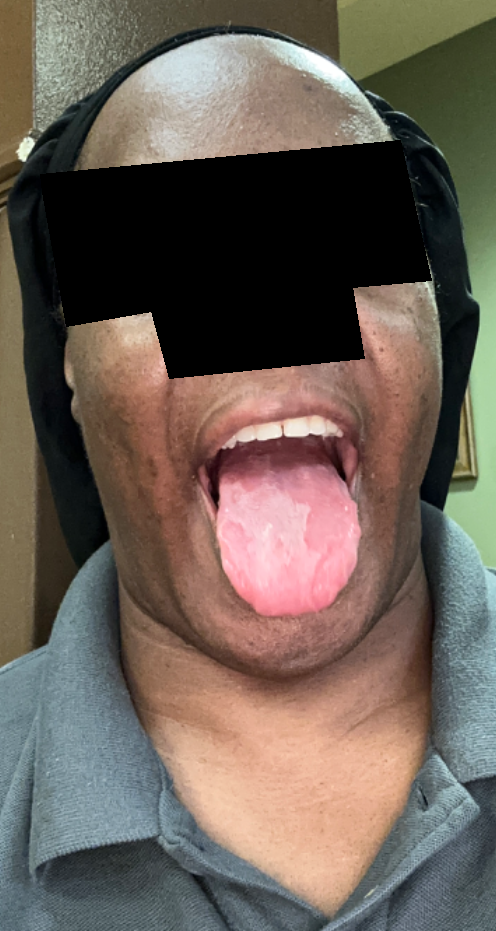view = at a distance
described texture = raised or bumpy
systemic symptoms = none reported
duration = less than one week
patient-reported symptoms = none reported
contributor = female, age 40–49
differential diagnosis = favoring Geographic tongue; with consideration of Atrophic glossitis; an alternative is Lichen planus/lichenoid eruption